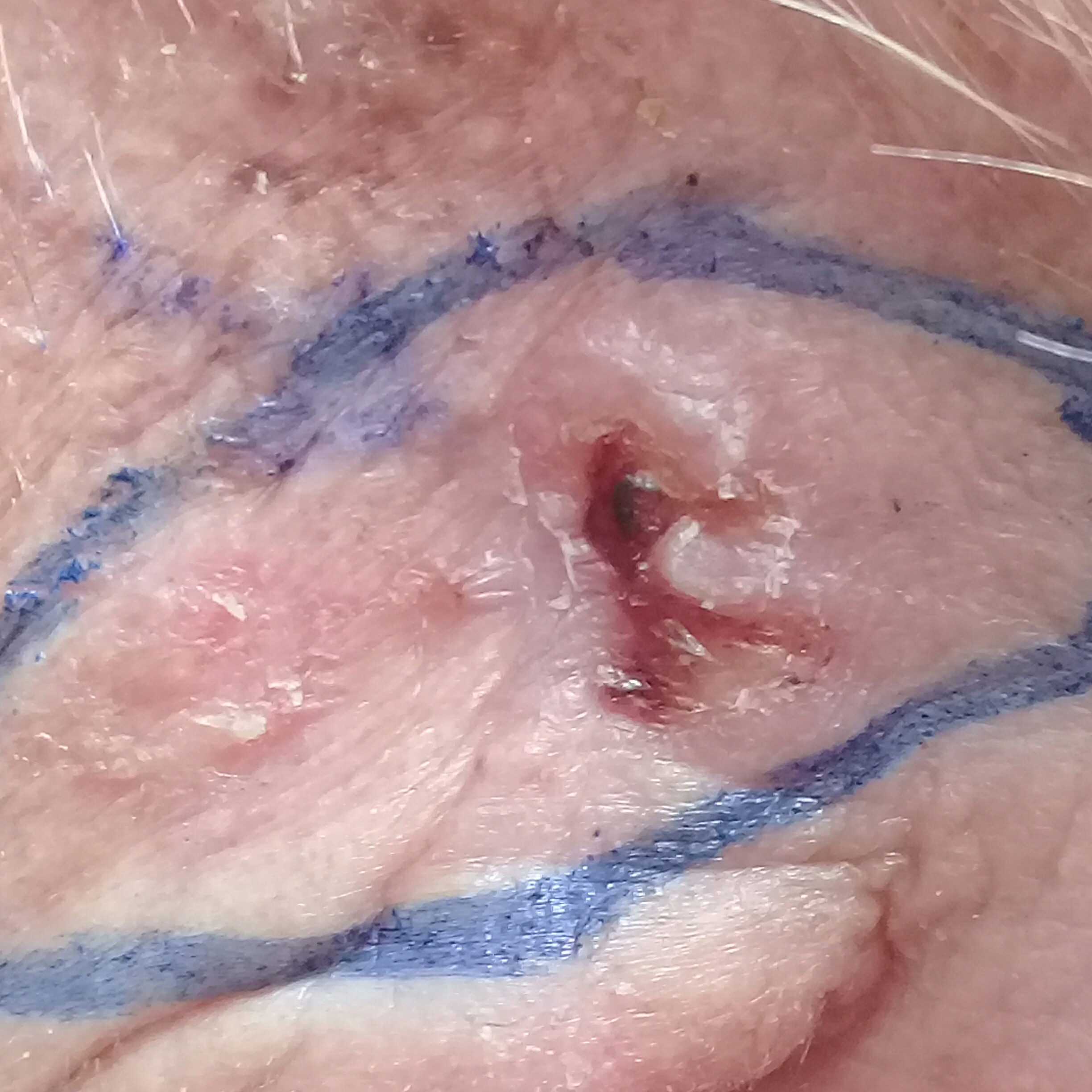patient — male, aged 83 | body site — an ear | patient-reported symptoms — elevation, pain, itching, bleeding | diagnostic label — basal cell carcinoma (biopsy-proven).